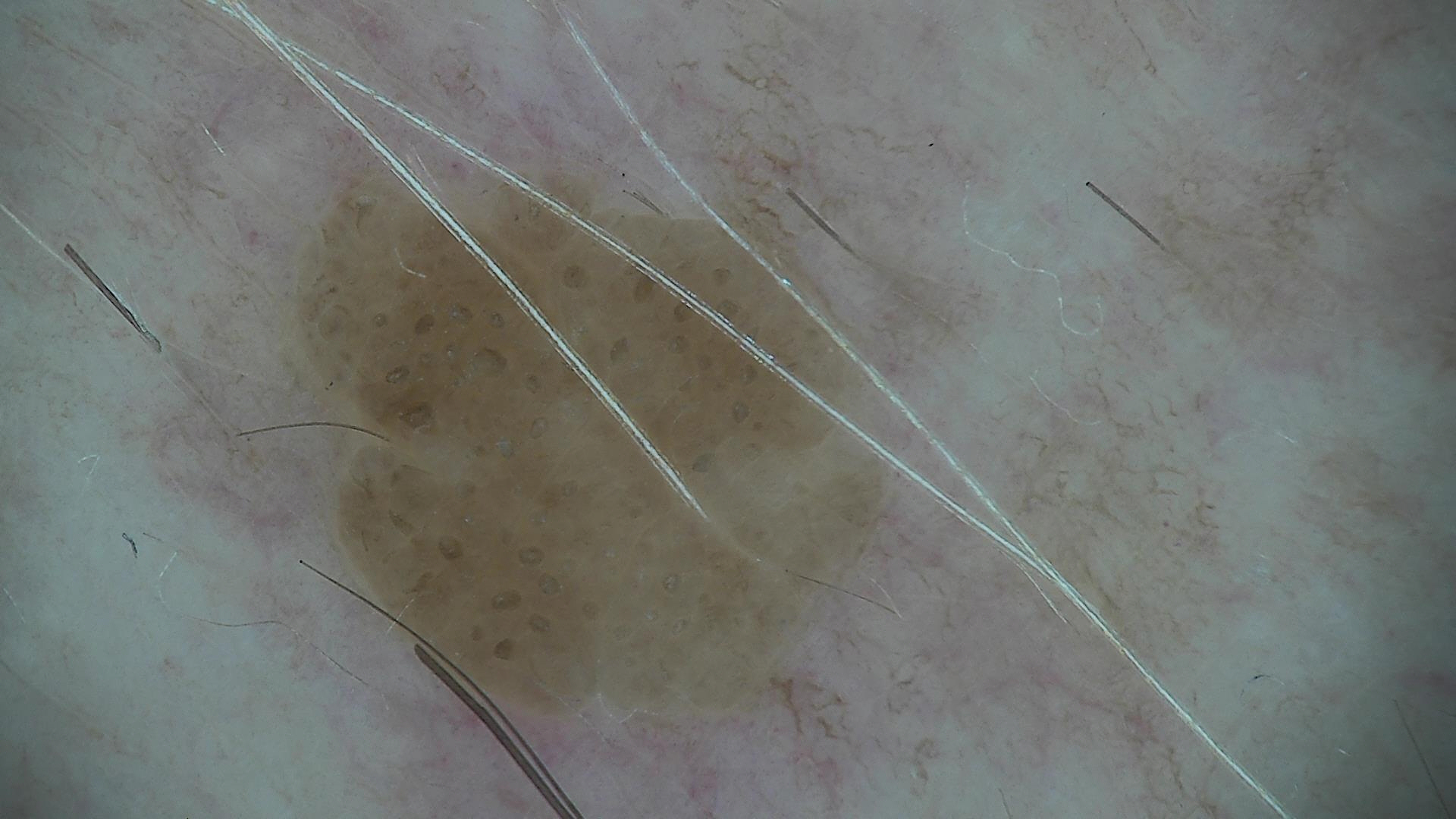  image: dermatoscopy
  diagnosis:
    name: seborrheic keratosis
    code: sk
    malignancy: benign
    super_class: non-melanocytic
    confirmation: expert consensus